A dermoscopic close-up of a skin lesion: 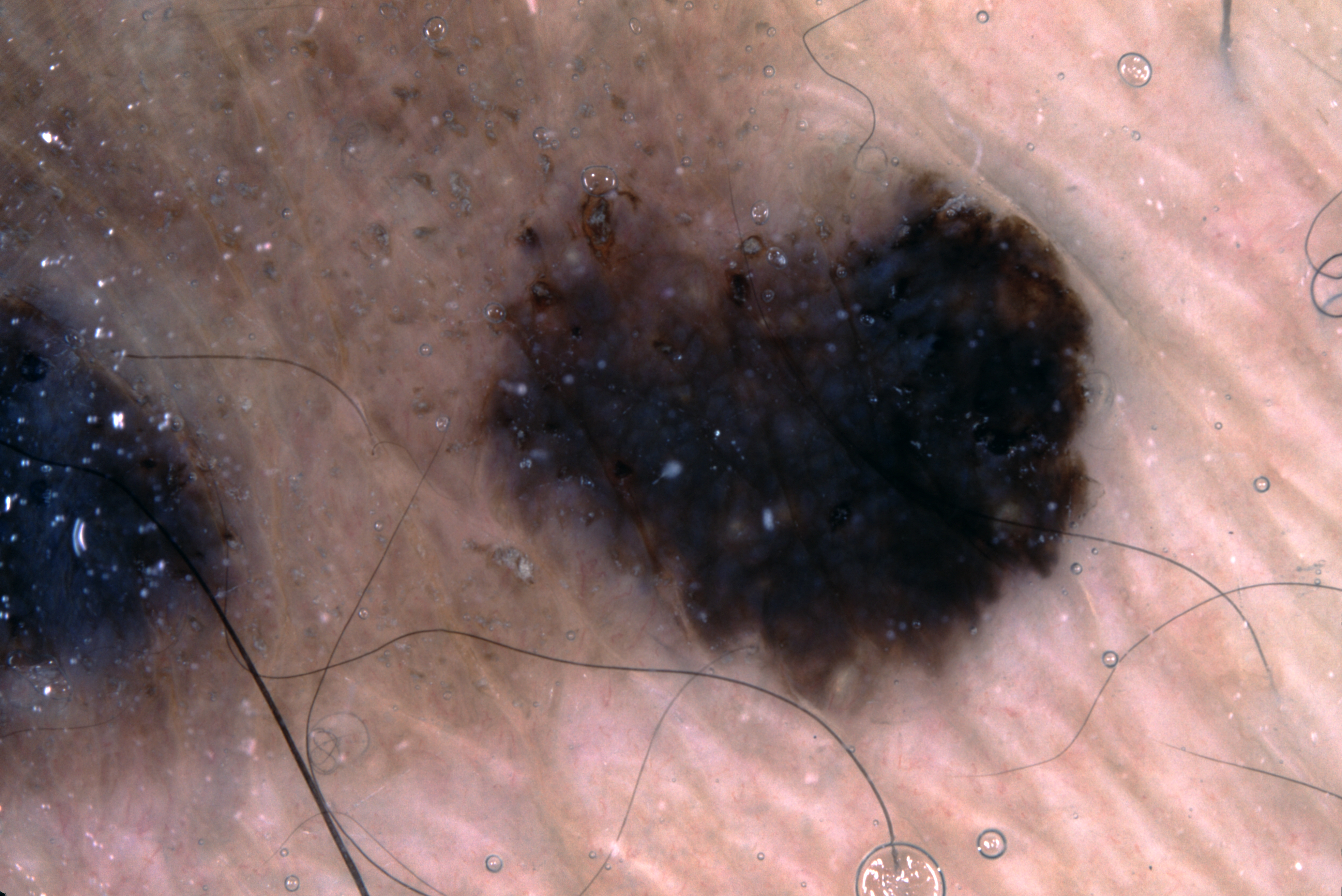dermoscopic findings: streaks and milia-like cysts; lesion location: extends across the entire field of view; diagnosis: a seborrheic keratosis, a keratinocytic lesion.